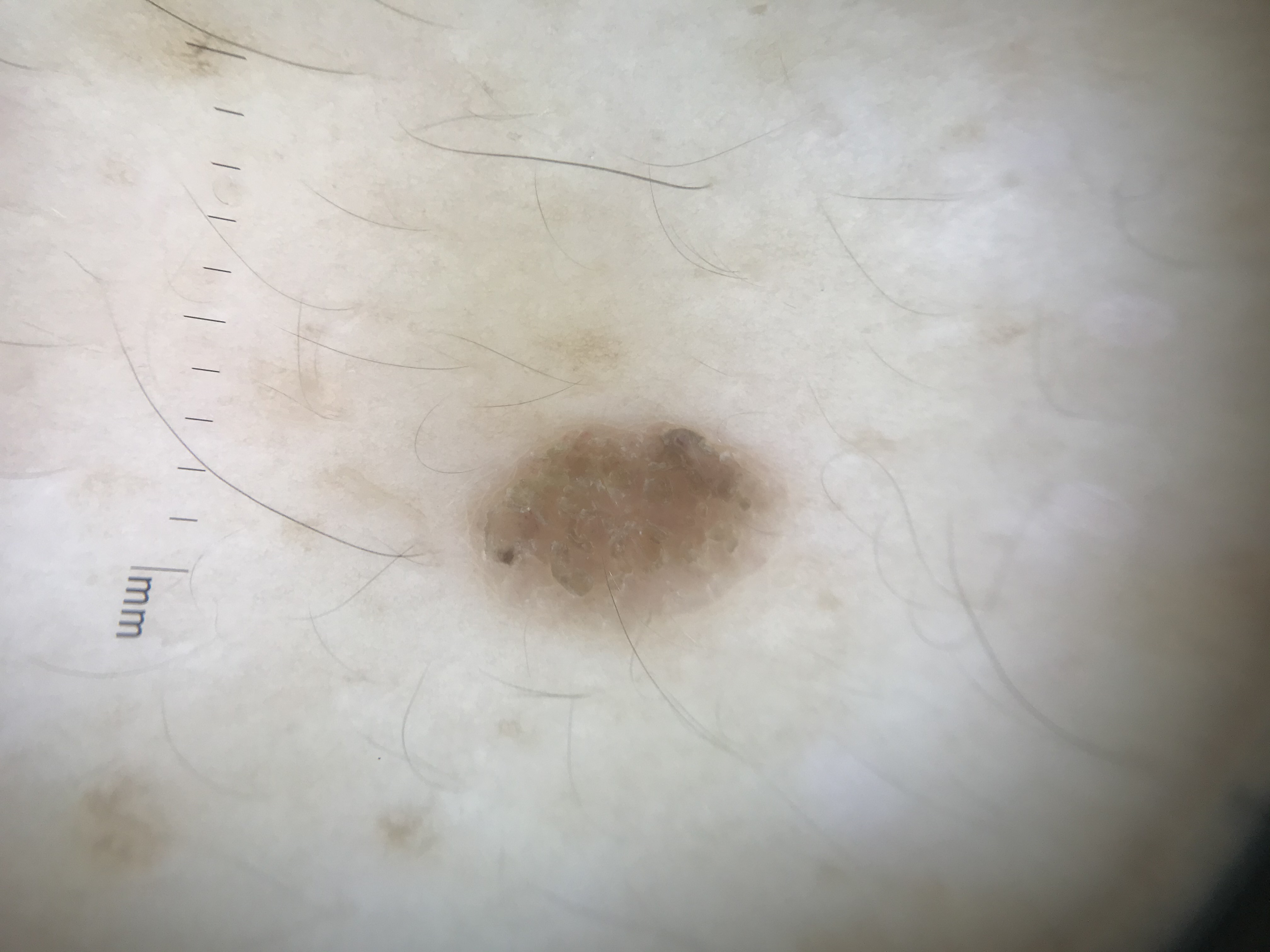Findings:
A dermoscopic photograph of a skin lesion.
Impression:
Consistent with a keratinocytic, benign lesion — a seborrheic keratosis.